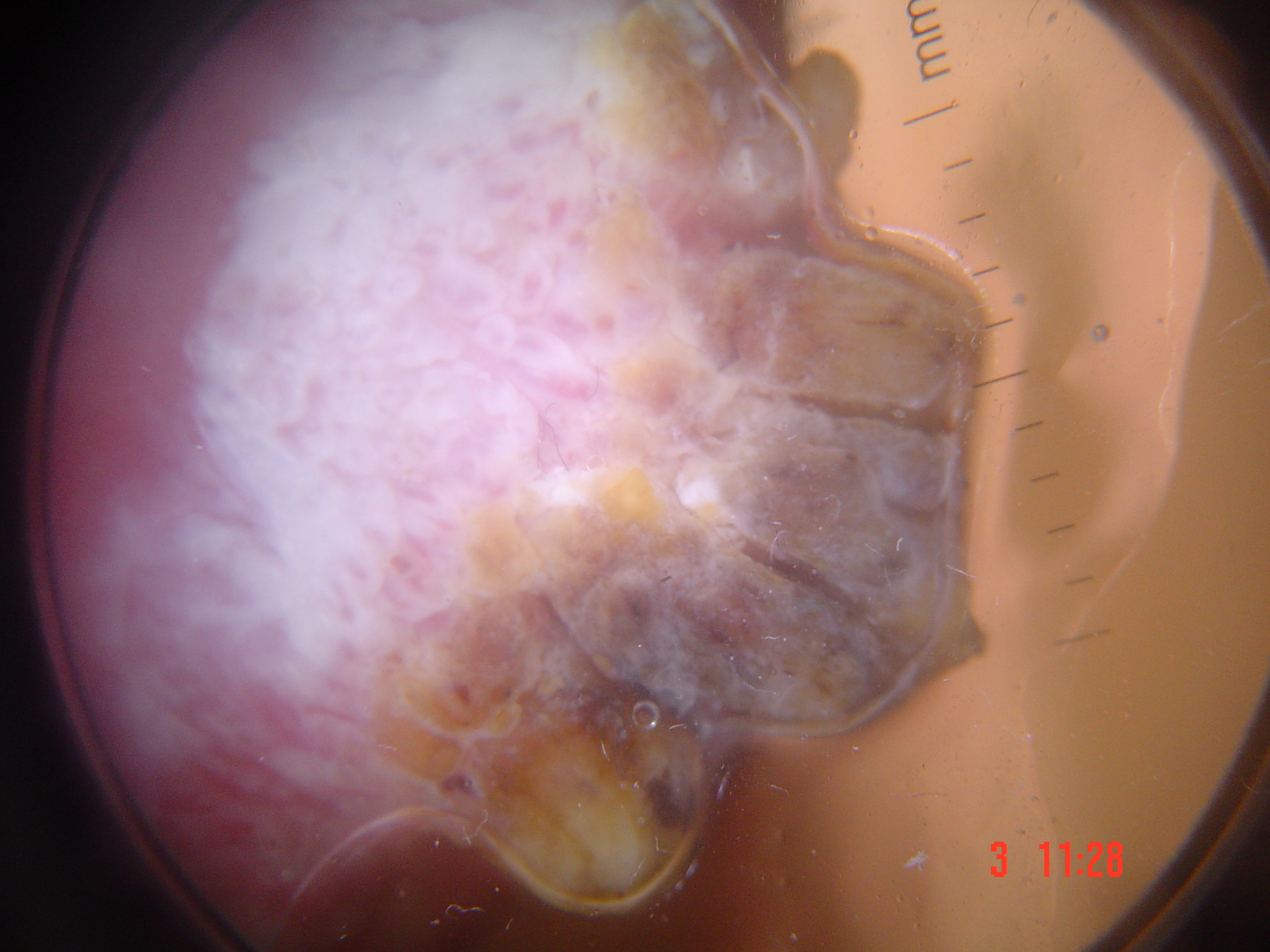A dermatoscopic image of a skin lesion. The architecture is that of a keratinocytic lesion. Biopsy-confirmed as a squamous cell carcinoma.